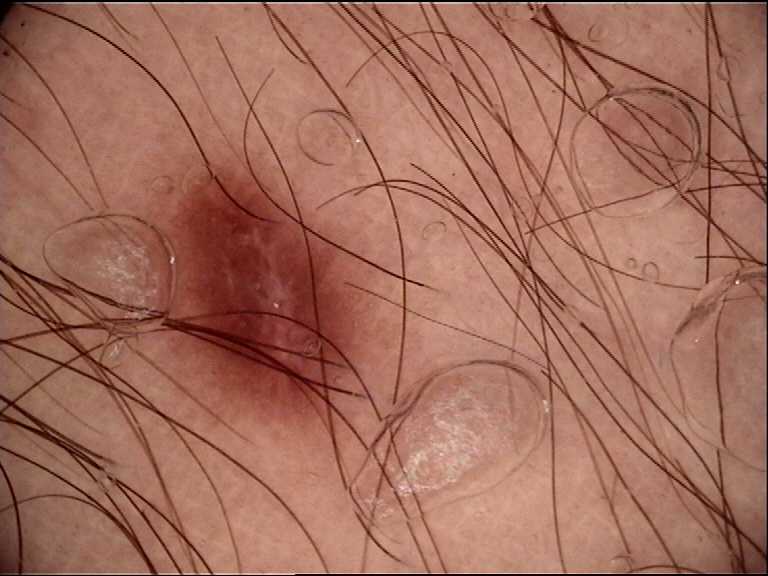assessment: dysplastic junctional nevus (expert consensus)